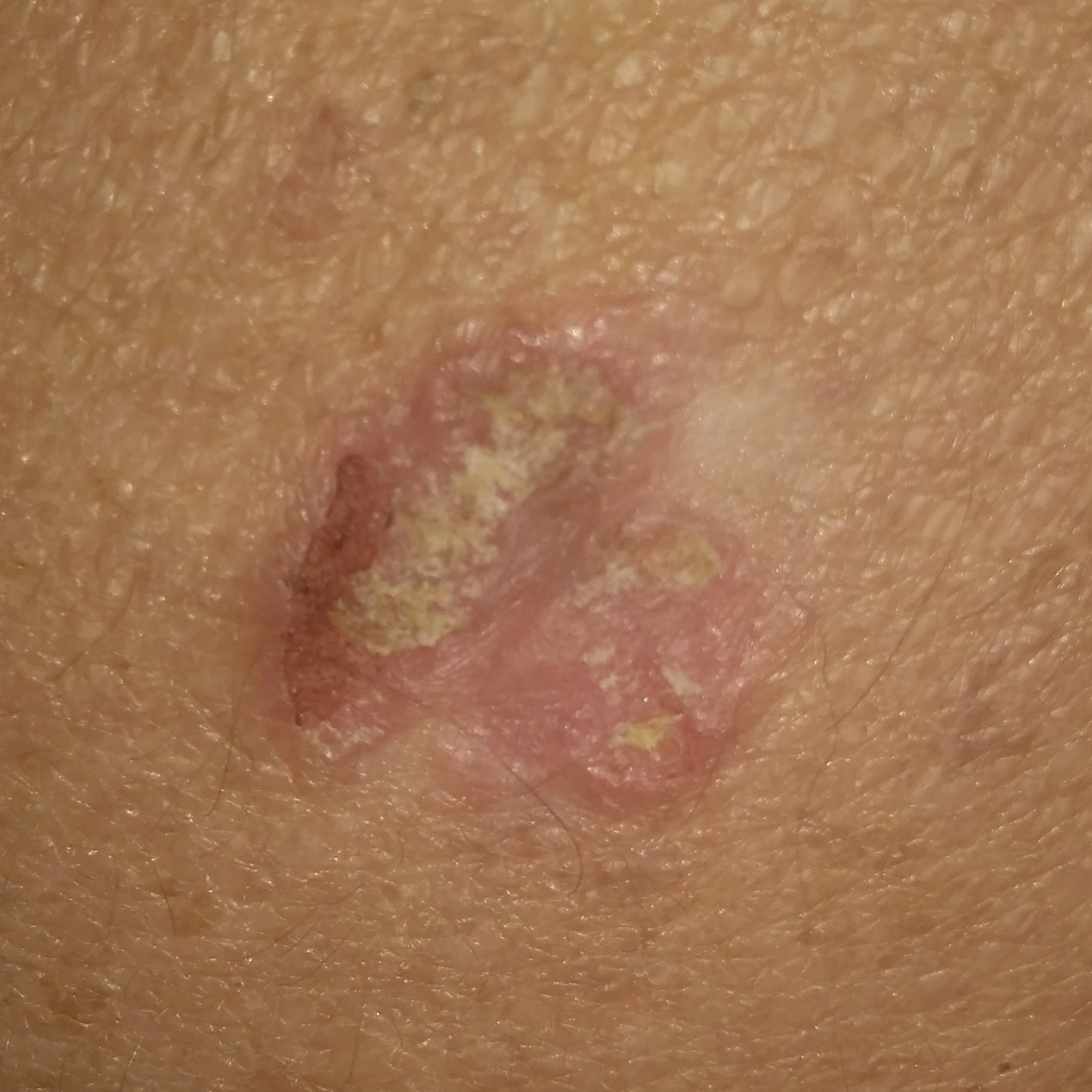subject: male, 70 years old
modality: clinical photo
body site: the back
patient-reported symptoms: growth, itching, pain, elevation / no bleeding
diagnosis: squamous cell carcinoma (biopsy-proven)